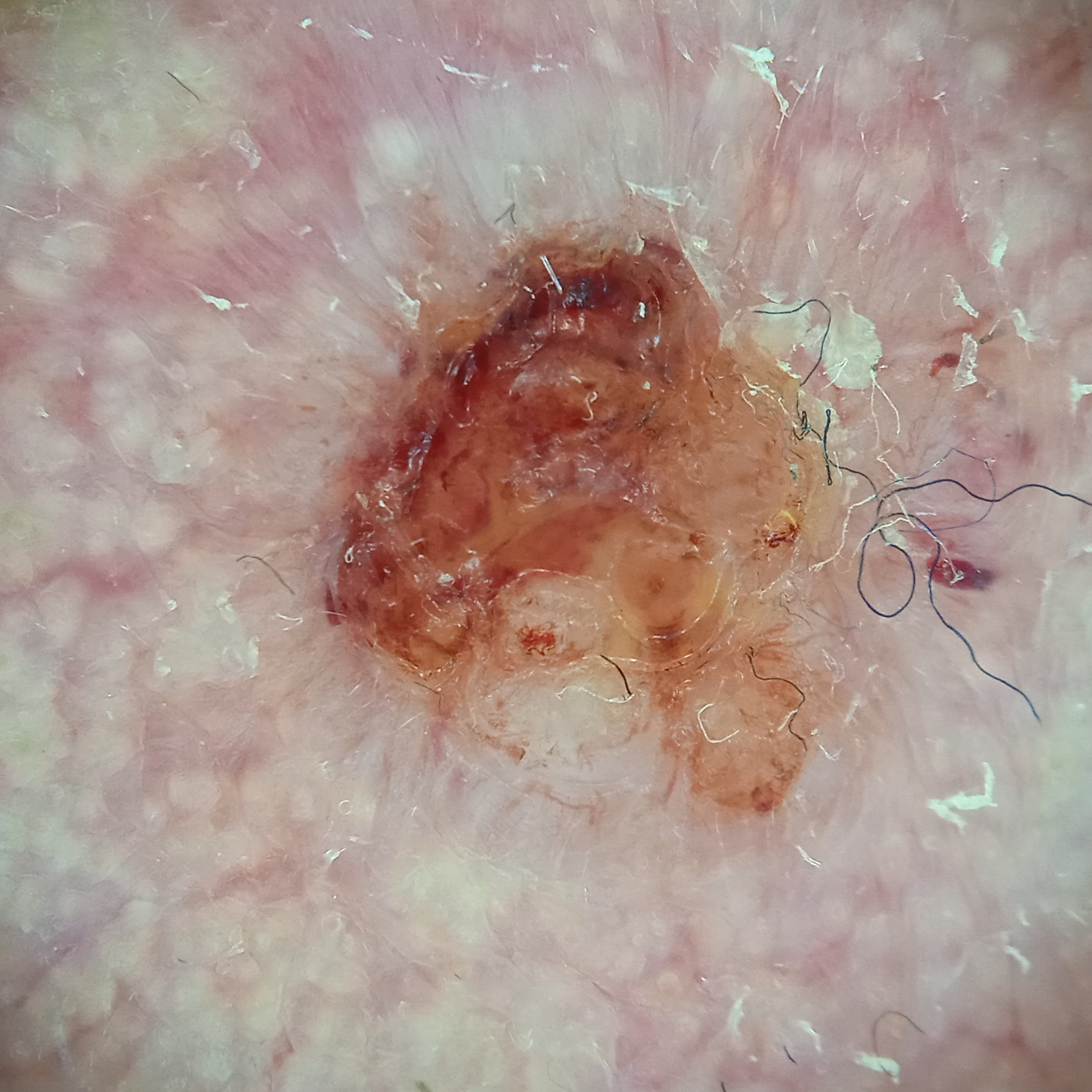Summary: The referring clinician suspected basal cell carcinoma. A male patient aged 89. A dermatoscopic image of a skin lesion. The patient says their skin reddens painfully with sun exposure. Located on the face. The lesion is about 8.5 mm across. Pathology: The biopsy diagnosis was a basal cell carcinoma, following excision, with a measured thickness of 2.2 mm.